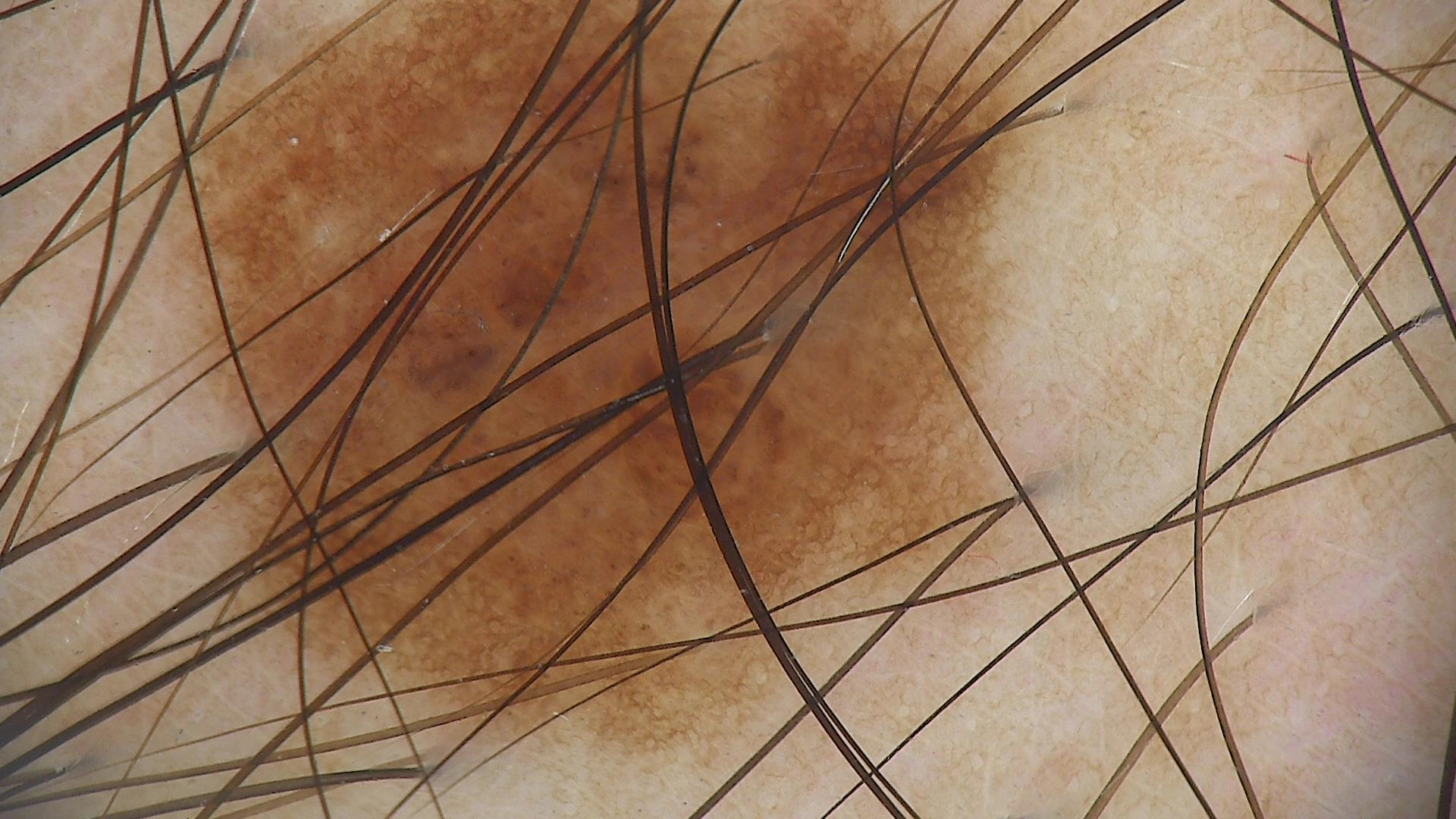Impression: Consistent with a dysplastic junctional nevus.